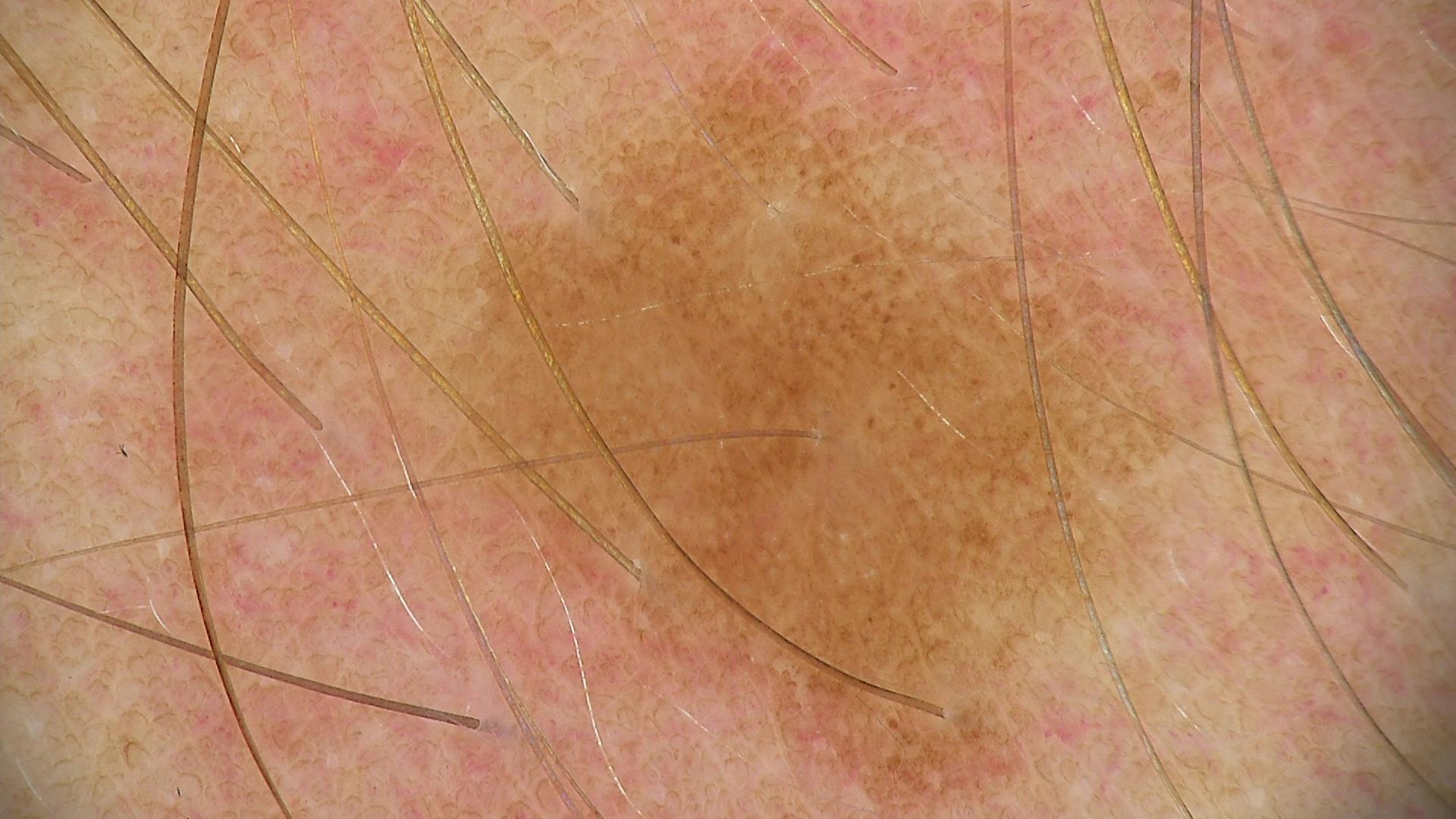image = dermatoscopy | label = dysplastic junctional nevus (expert consensus).